A male subject roughly 70 years of age. A dermoscopy image of a single skin lesion.
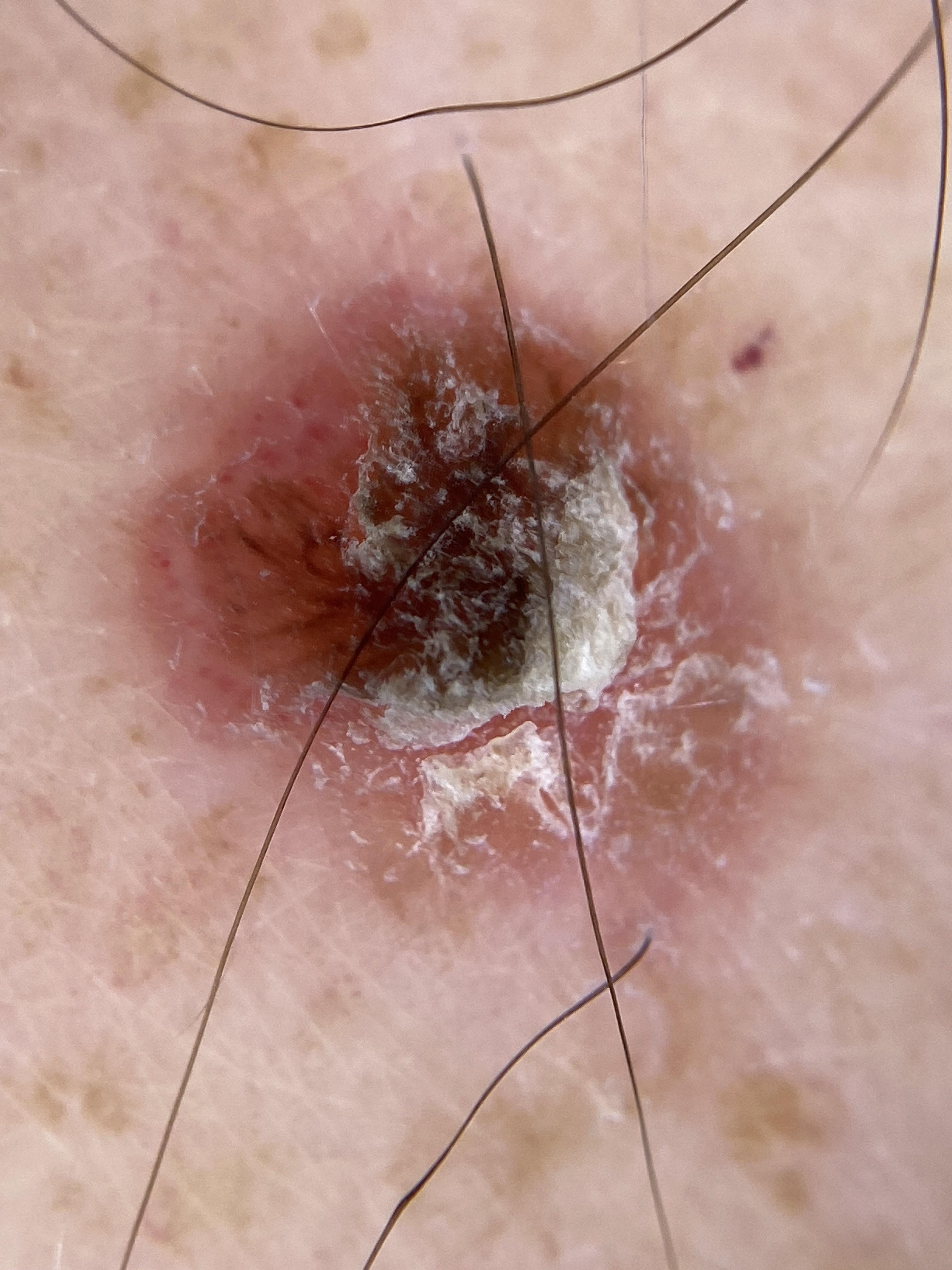Q: Where on the body is the lesion?
A: an upper extremity
Q: What did the workup show?
A: Squamous cell carcinoma (biopsy-proven)